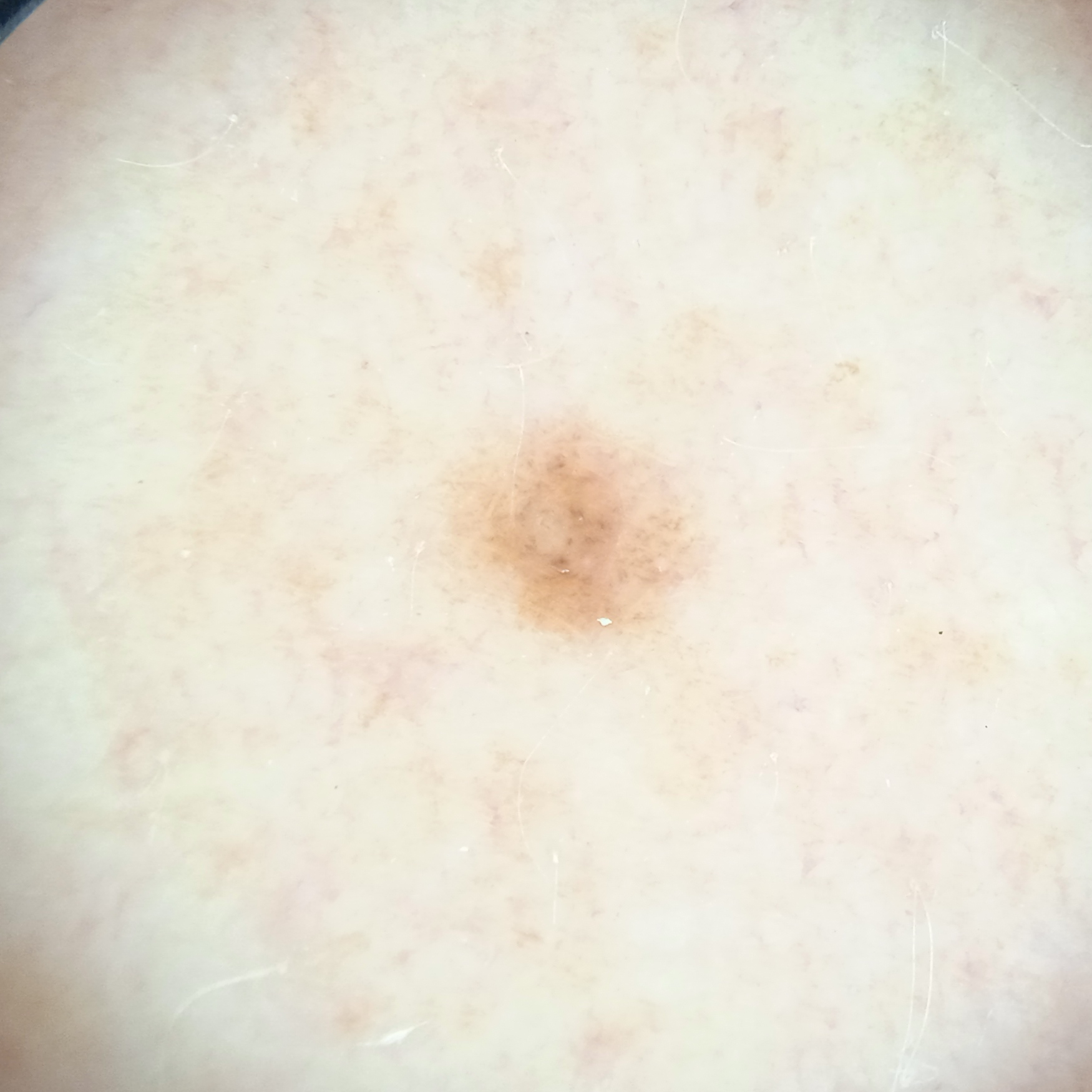<case>
<diagnosis>
<name>melanocytic nevus</name>
<malignancy>benign</malignancy>
</diagnosis>
</case>